The patient was assessed as Fitzpatrick II. By history, prior skin cancer (patient or family). A male subject in their mid-50s. A clinical photograph showing a skin lesion:
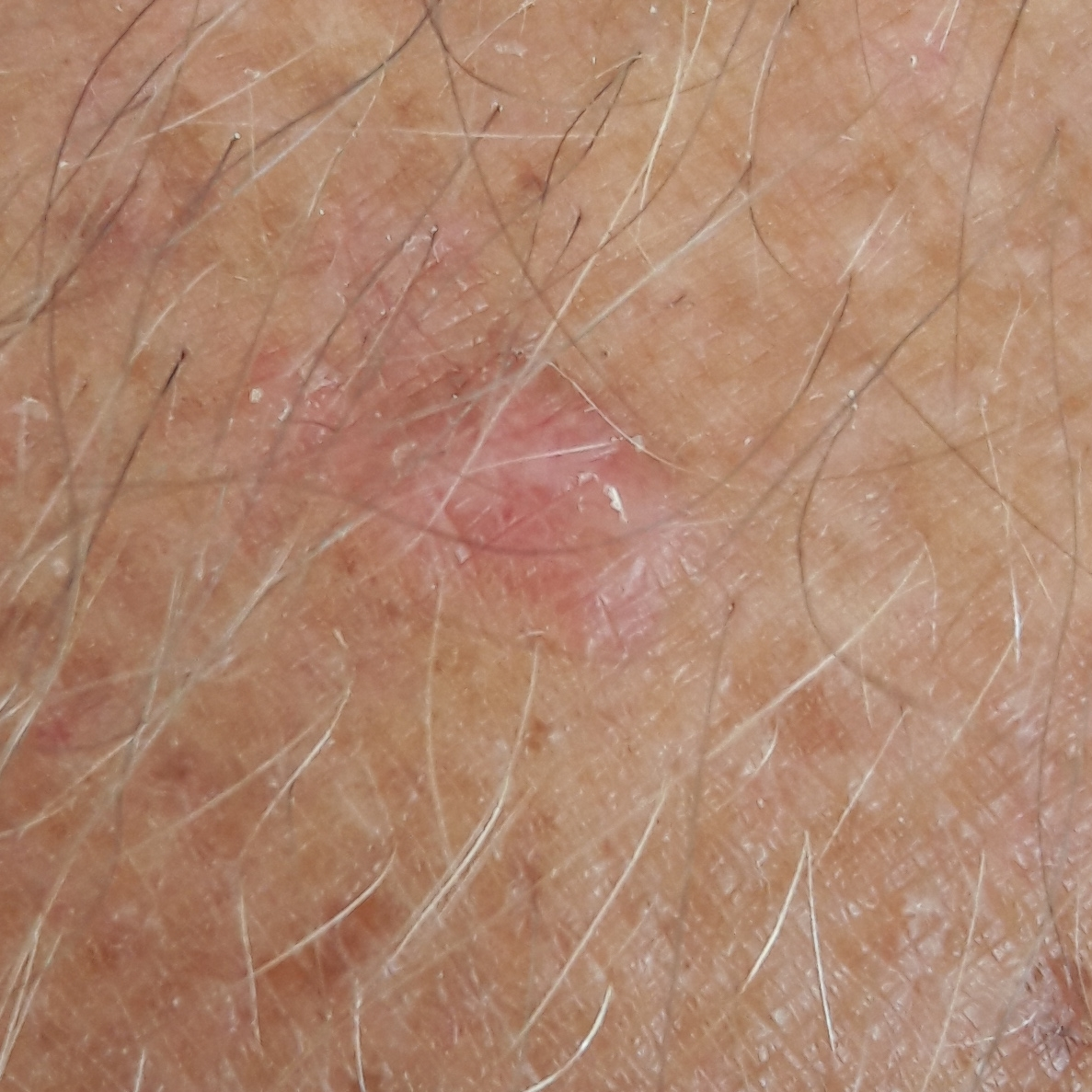The lesion was found on a forearm. The lesion is roughly 5 by 5 mm. Per patient report, the lesion is elevated. The biopsy diagnosis was a malignancy — a basal cell carcinoma.